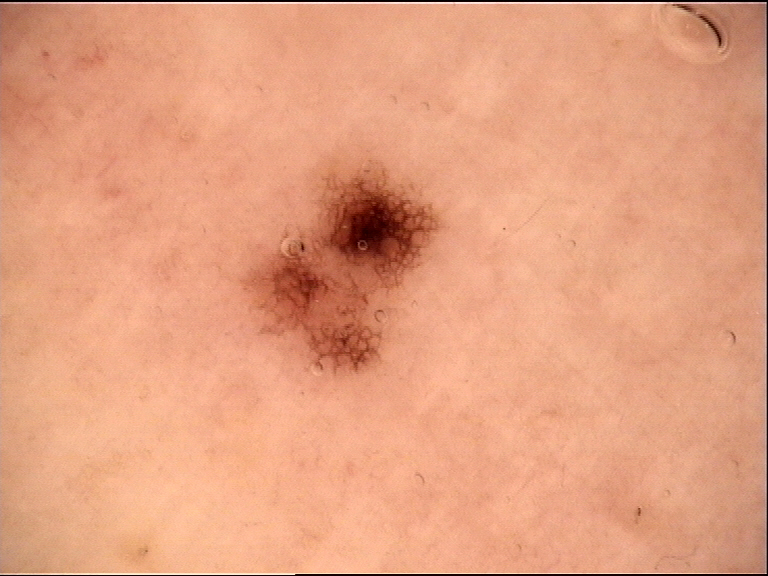Conclusion: Consistent with a dysplastic junctional nevus.